The subject is a male aged approximately 45. A dermoscopic close-up of a skin lesion — 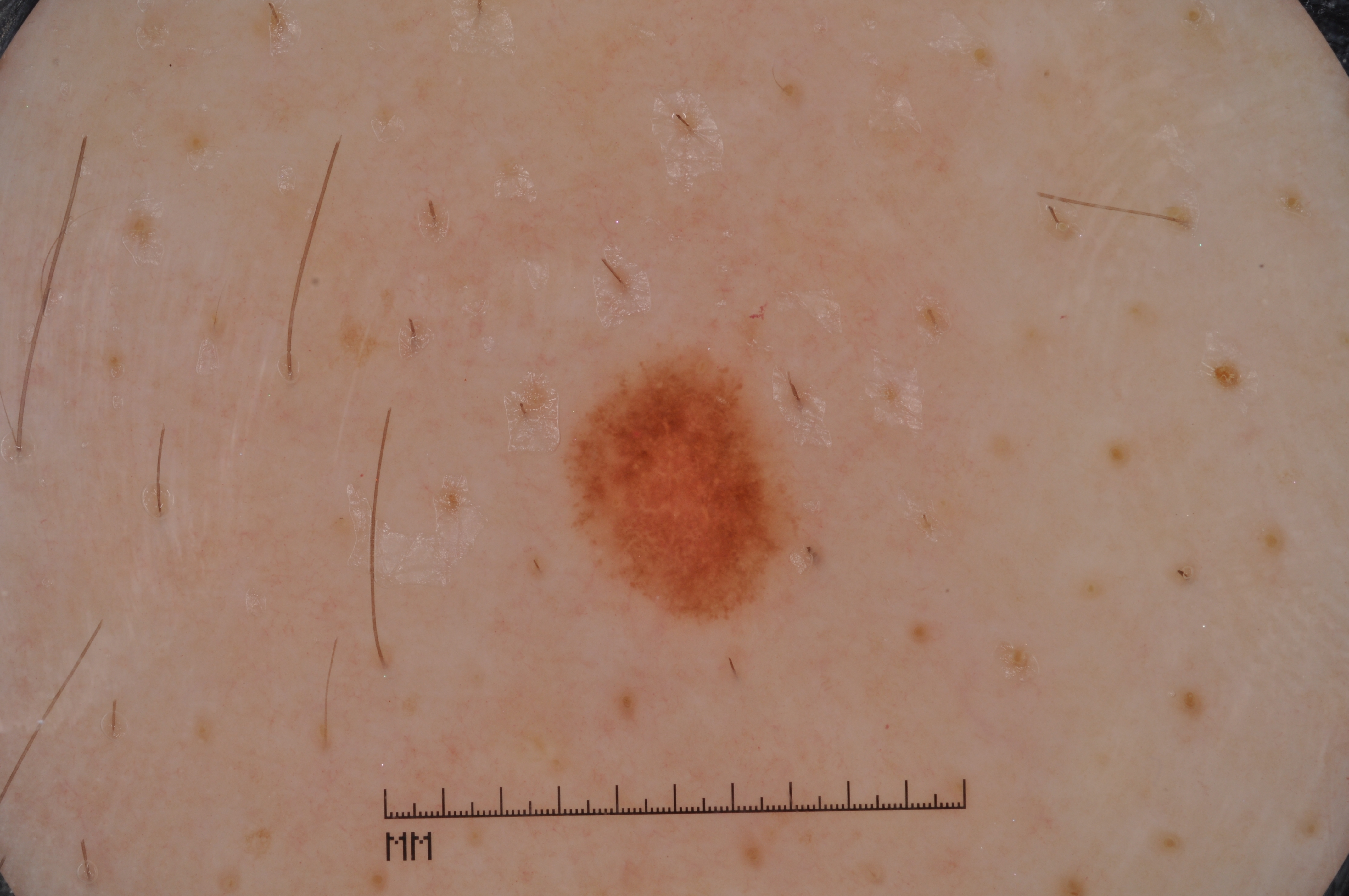Dermoscopically, the lesion shows negative network. The lesion's extent is left=569, top=357, right=801, bottom=616. The diagnostic assessment was a melanocytic nevus.